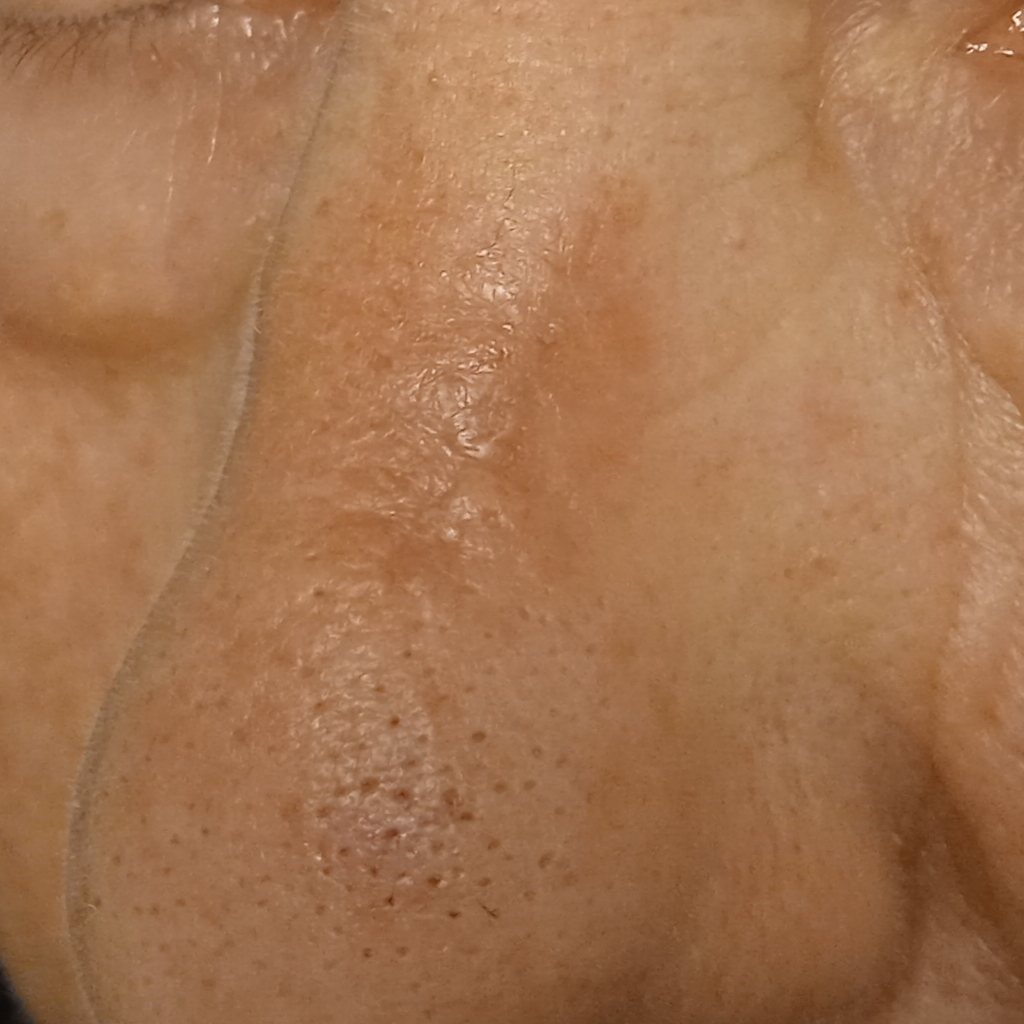– nevus count — few melanocytic nevi overall
– modality — clinical photograph
– patient — female, 68 years of age
– sun reaction — skin tans without first burning
– anatomic site — the face
– lesion size — 9.9 mm
– diagnostic label — actinic keratosis (dermatologist consensus)